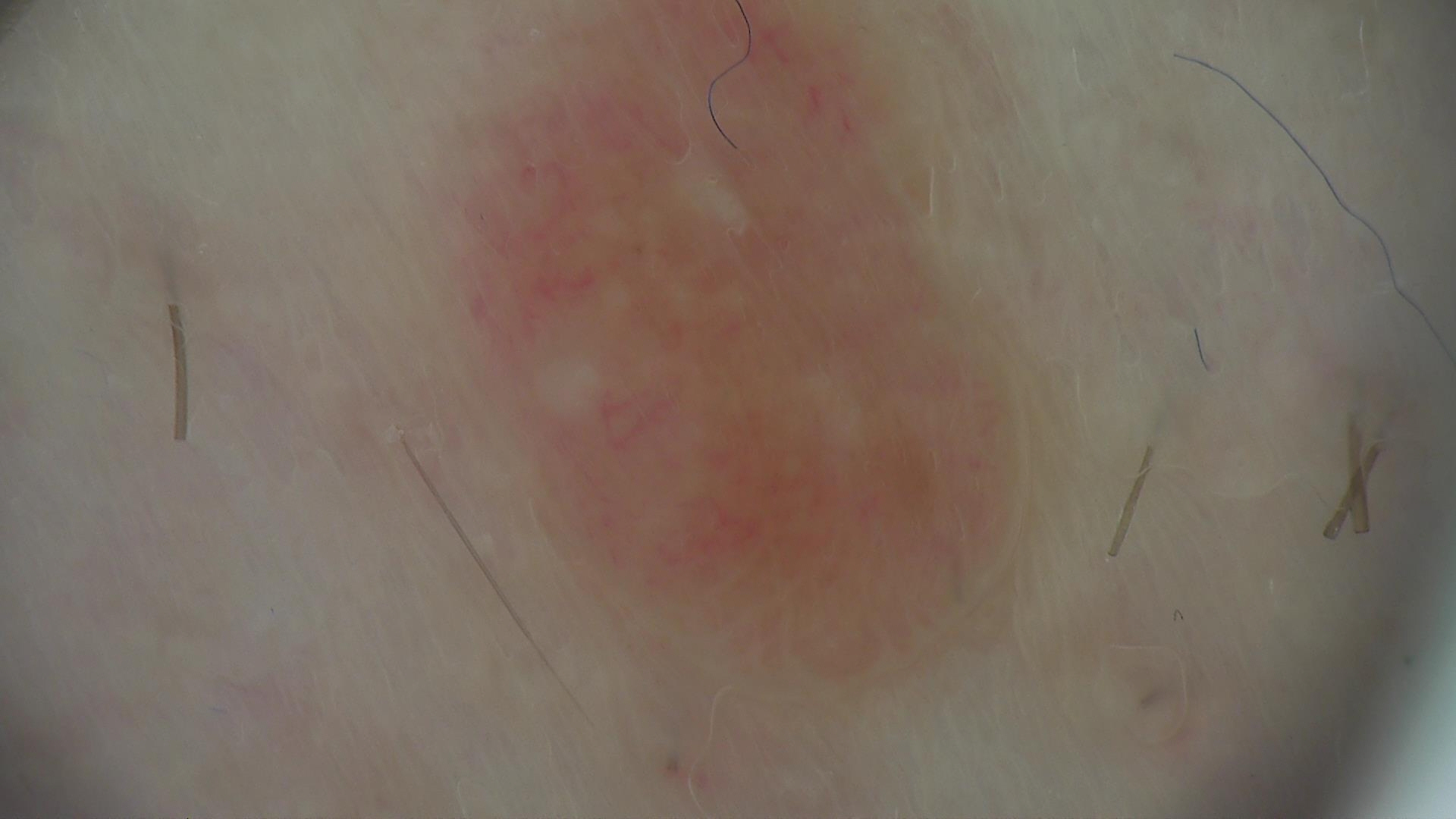classification: banal; diagnostic label: dermal nevus (expert consensus).